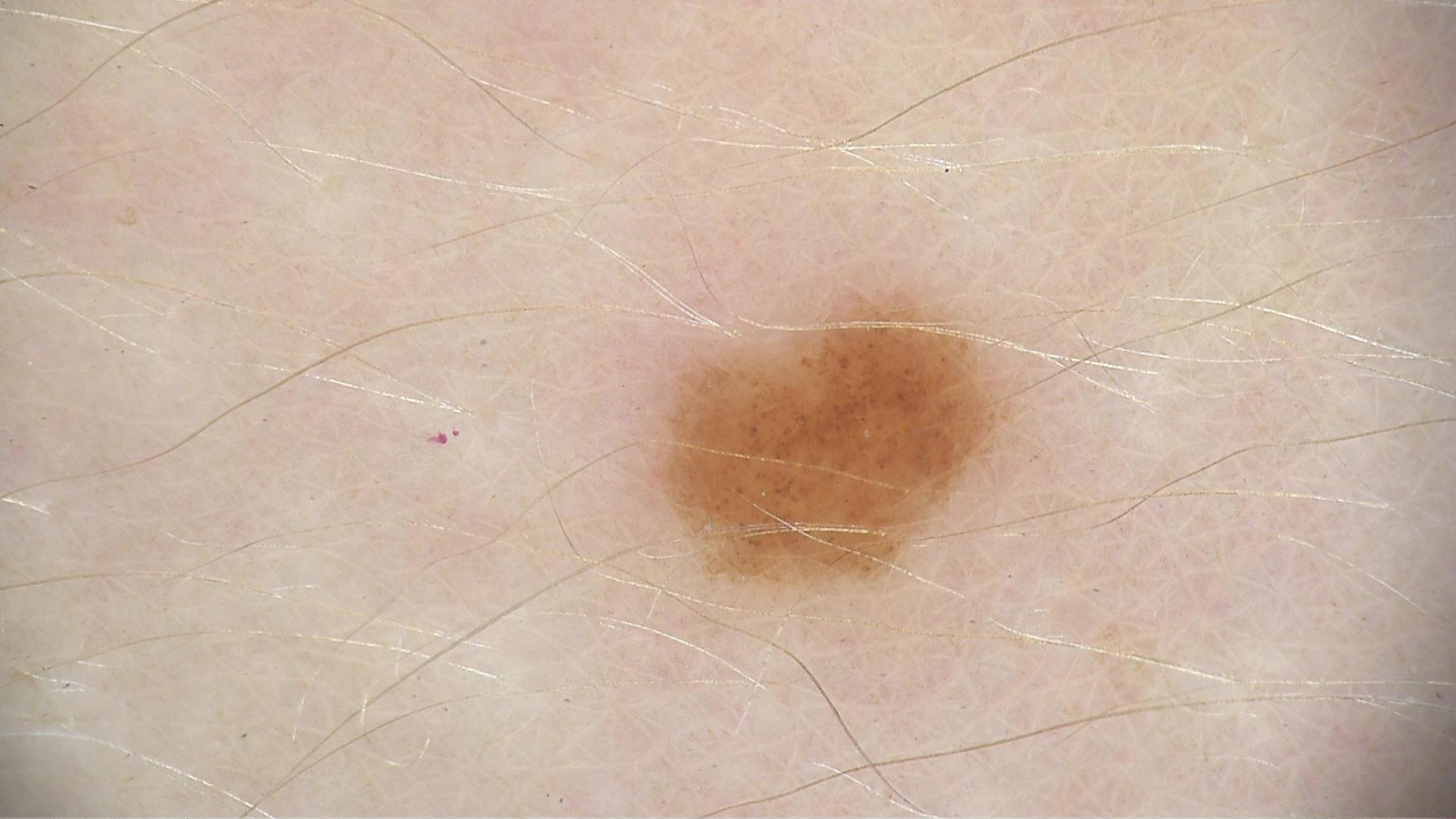<dermoscopy>
  <image>dermatoscopy</image>
  <diagnosis>
    <name>dysplastic junctional nevus</name>
    <code>jd</code>
    <malignancy>benign</malignancy>
    <super_class>melanocytic</super_class>
    <confirmation>expert consensus</confirmation>
  </diagnosis>
</dermoscopy>